The condition has been present for less than one week, the subject is male, the patient described the issue as a rash, this image was taken at an angle, texture is reported as rough or flaky and raised or bumpy, the affected area is the leg and arm, FST III, the patient notes itching.
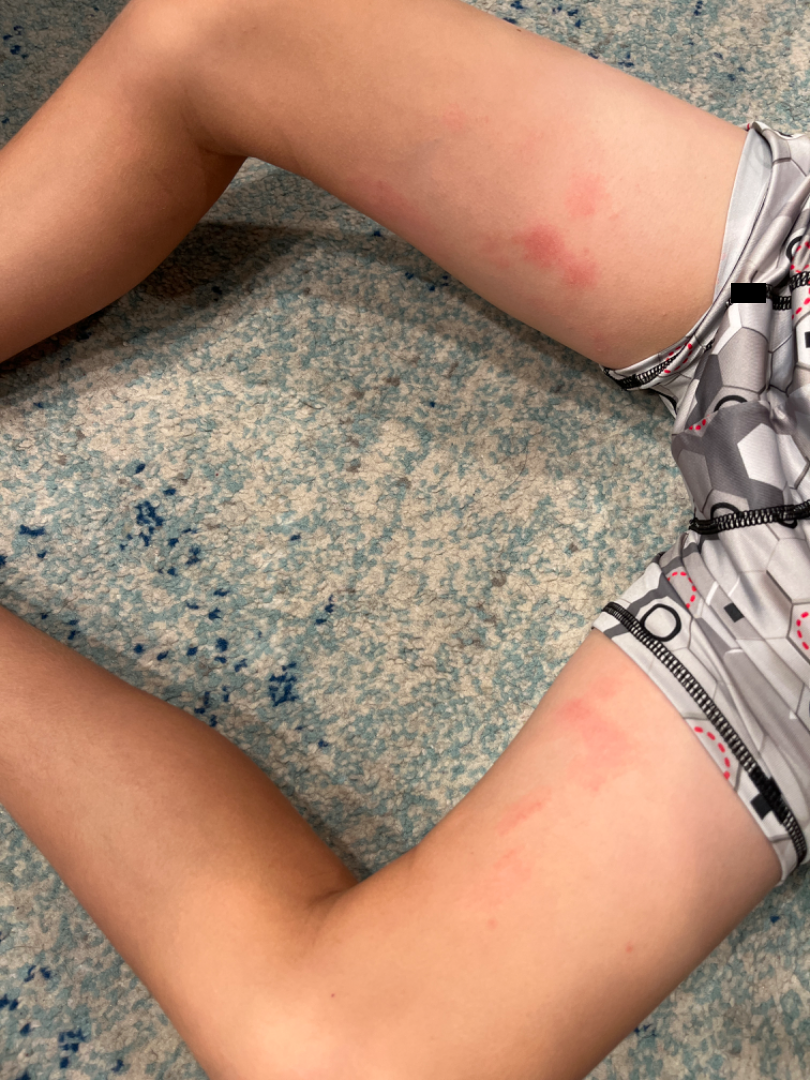Assessment:
Eczema (most likely); Irritant Contact Dermatitis (considered).